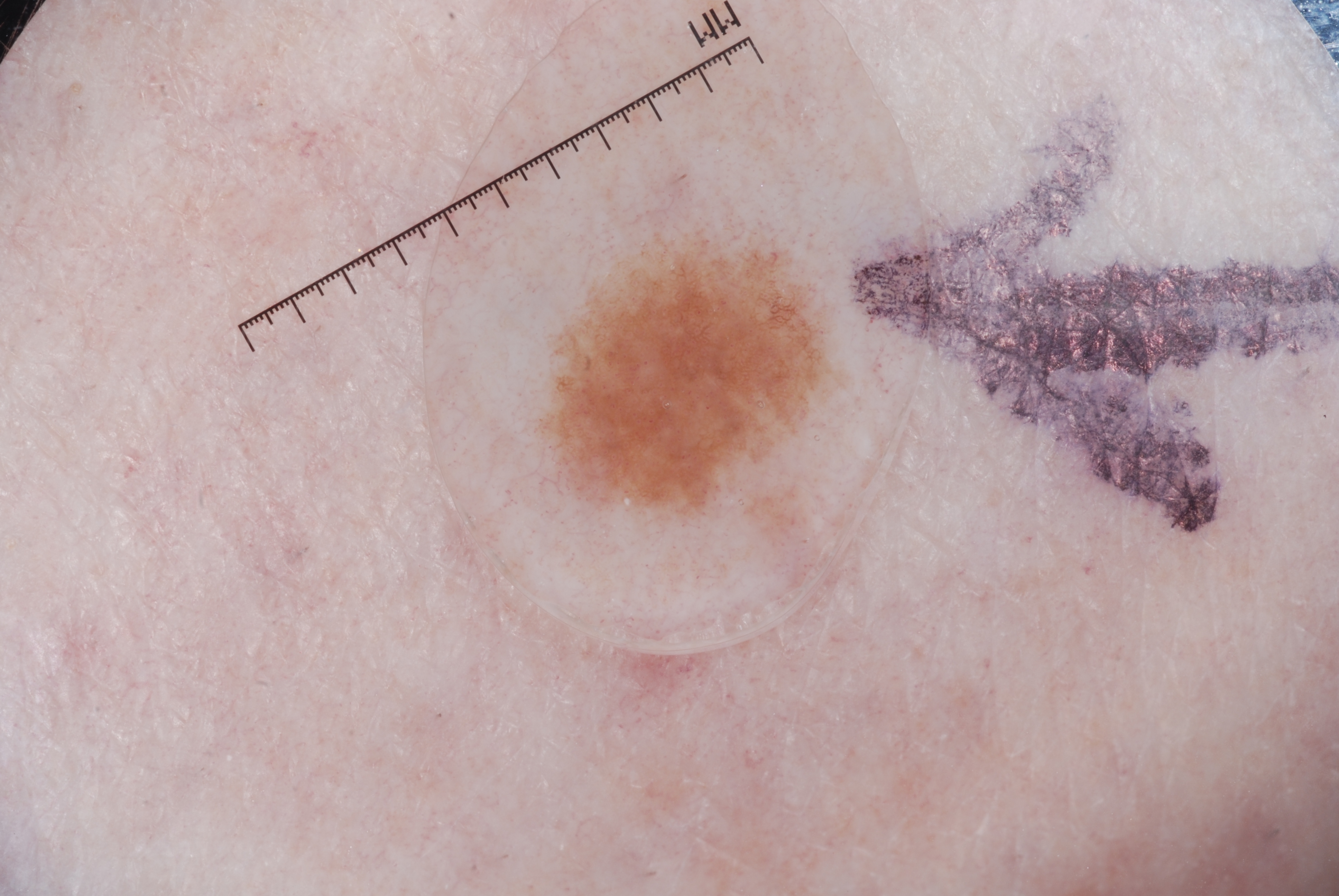{"image": {"modality": "dermoscopy"}, "lesion_extent": {"approx_field_fraction_pct": 5}, "dermoscopic_features": {"present": ["pigment network"], "absent": ["milia-like cysts", "streaks", "negative network"]}, "lesion_location": {"bbox_xyxy": [534, 228, 843, 526]}, "diagnosis": {"name": "melanocytic nevus", "malignancy": "benign", "lineage": "melanocytic", "provenance": "clinical"}}